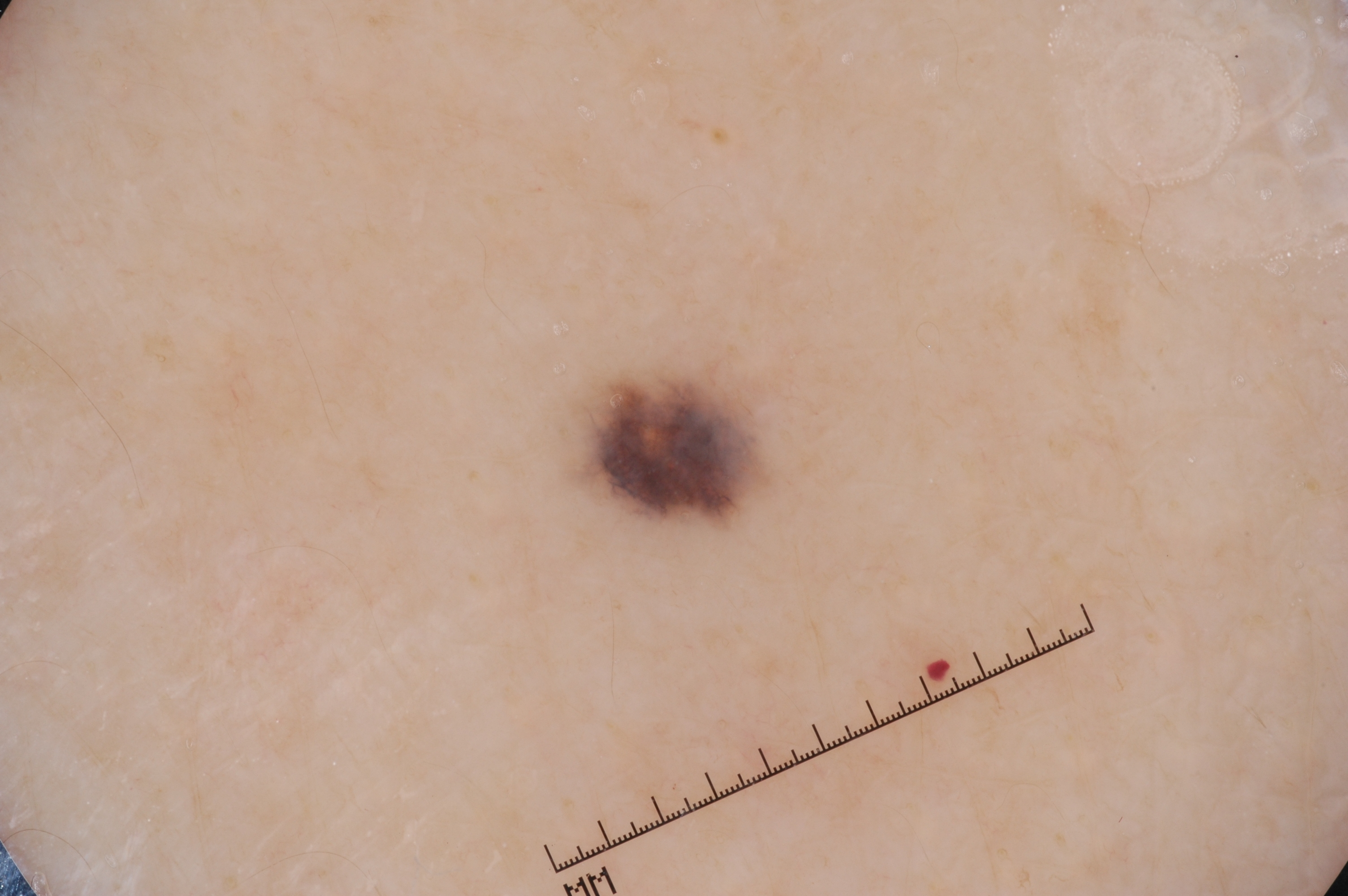Notes:
* imaging — dermoscopy
* subject — female, roughly 75 years of age
* dermoscopic pattern — pigment network; absent: negative network, milia-like cysts, and streaks
* bounding box — <box>569, 364, 779, 525</box>
* impression — a melanocytic nevus